Dermoscopy of a skin lesion.
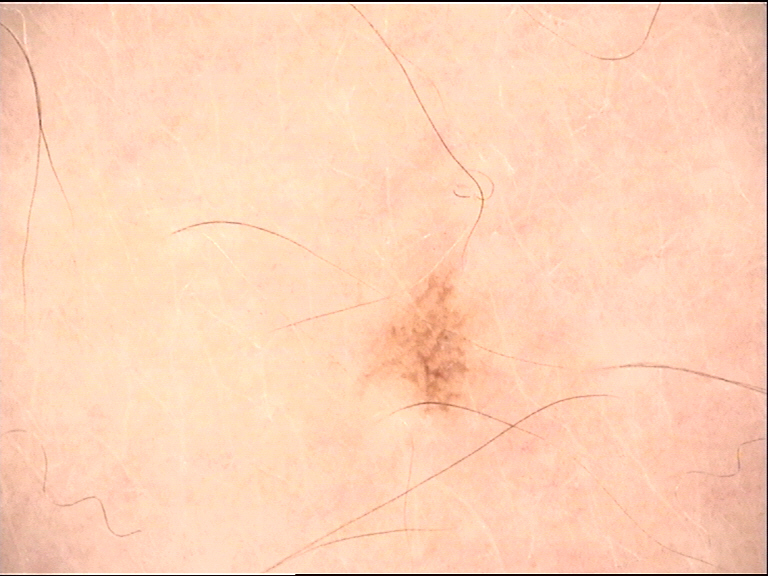category = banal; label = junctional nevus (expert consensus).